This is a close-up image; the lesion involves the head or neck; self-categorized by the patient as a rash; the lesion is associated with bothersome appearance, pain and burning; present for less than one week; the lesion is described as rough or flaky:
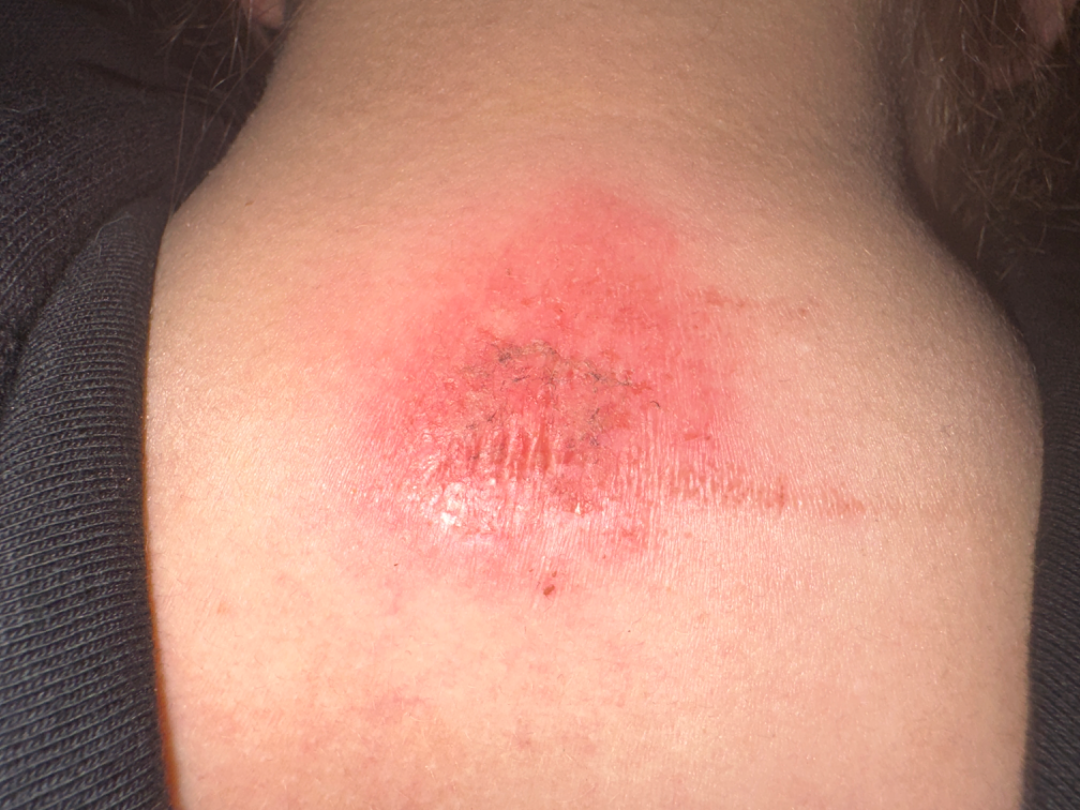differential diagnosis: favoring Eczema